A female patient, aged 28 to 32 · a dermatoscopic image of a skin lesion.
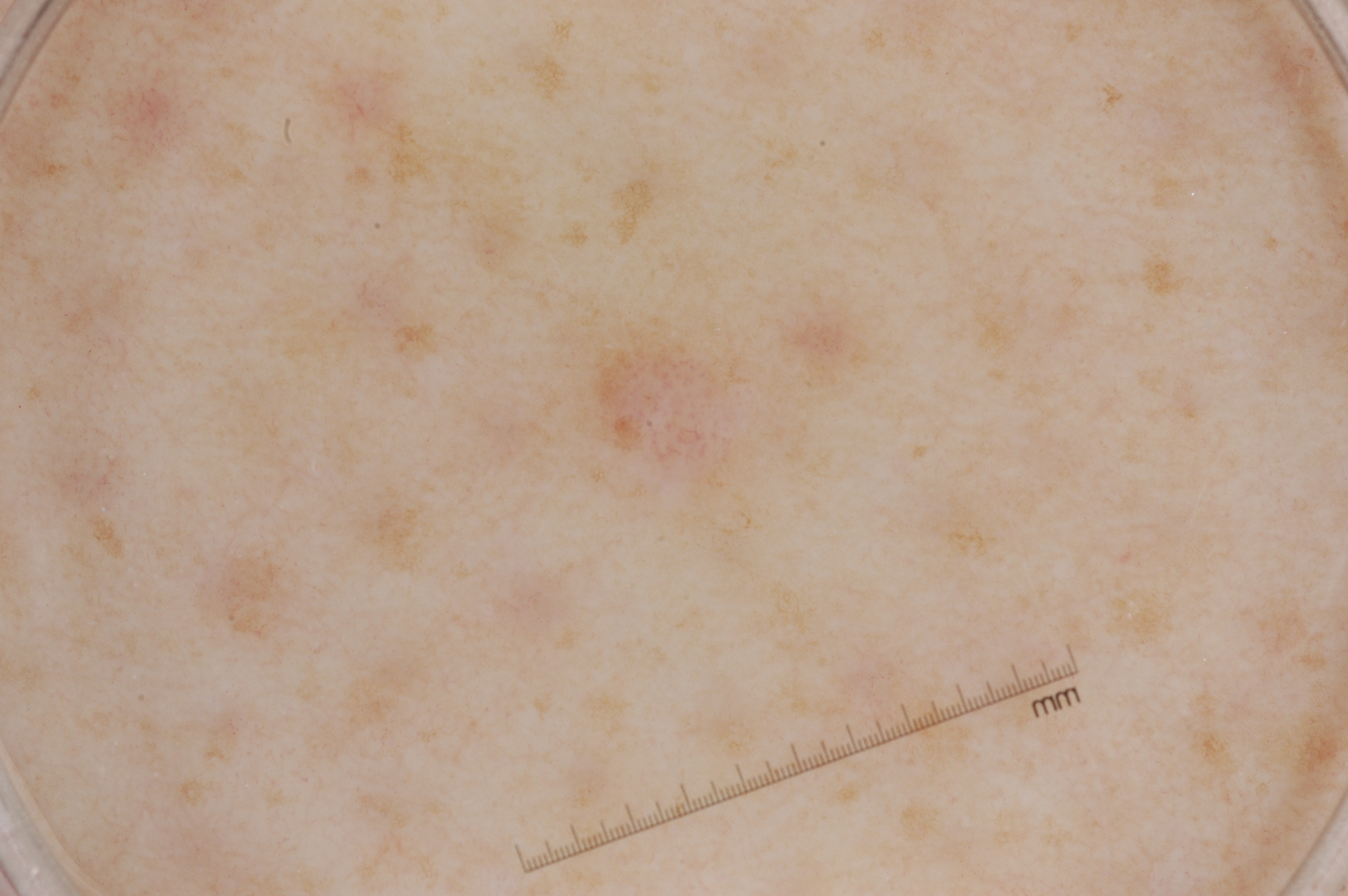On dermoscopy, the lesion shows no negative network, streaks, milia-like cysts, or pigment network. Lesion location: 578/342/773/489. The lesion takes up about 2% of the image. The clinical diagnosis was a melanocytic nevus.